A dermoscopic photograph of a skin lesion.
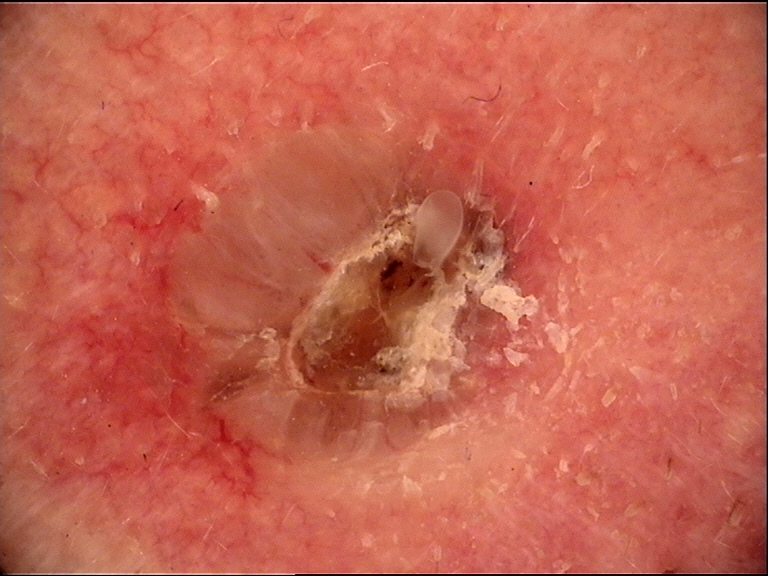Conclusion: The biopsy diagnosis was a malignant, keratinocytic lesion — a basal cell carcinoma.